A dermoscopic image of a skin lesion.
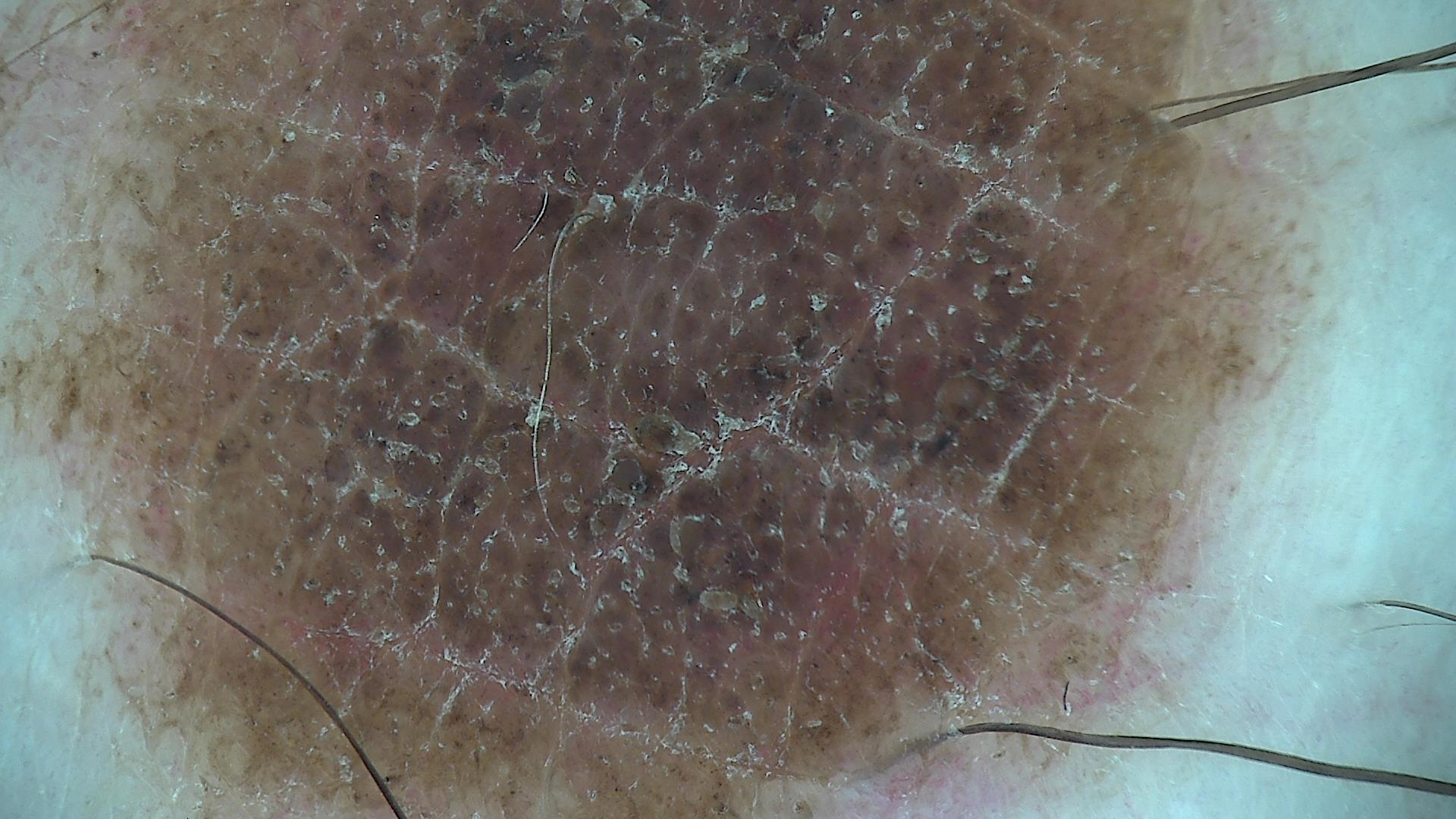Conclusion: The diagnosis was a banal lesion — a congenital compound nevus.